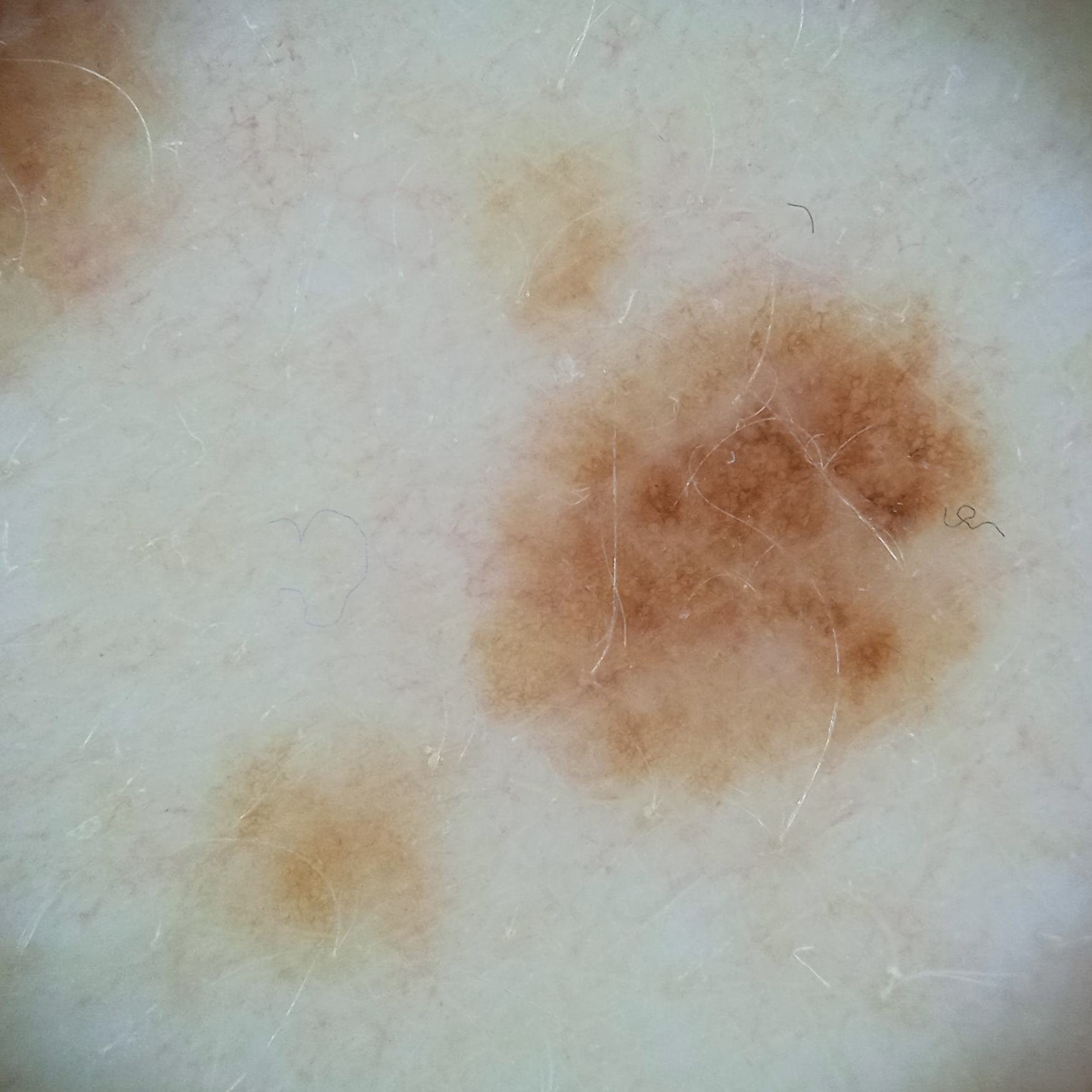Acquired for a research image collection, with no referral diagnosis.
A dermoscopic image of a skin lesion.
A female patient aged 54.
The lesion involves the back.
The lesion measures approximately 6.4 mm.
Dermatologist review favored an atypical (dysplastic) nevus.